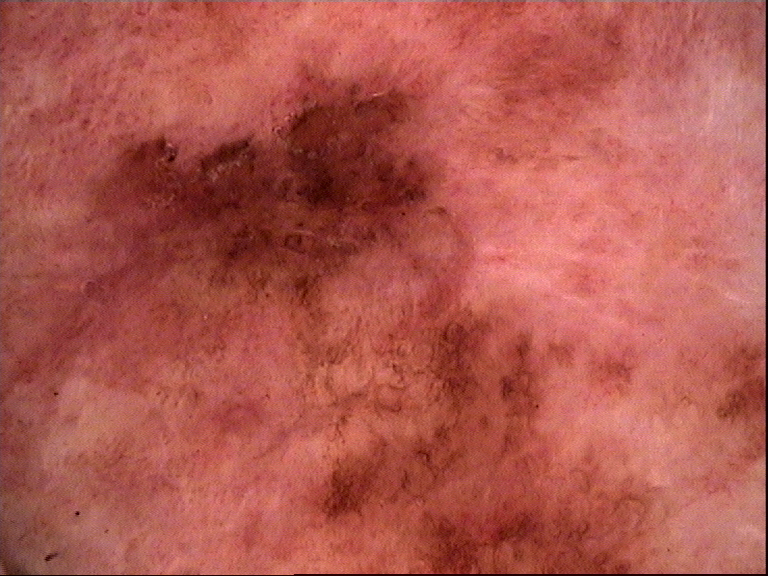imaging: dermatoscopy, diagnostic label: Bowen's disease (biopsy-proven).